FST II · a clinical close-up photograph of a skin lesion · by history, prior malignancy (patient or family), pesticide exposure, and alcohol use:
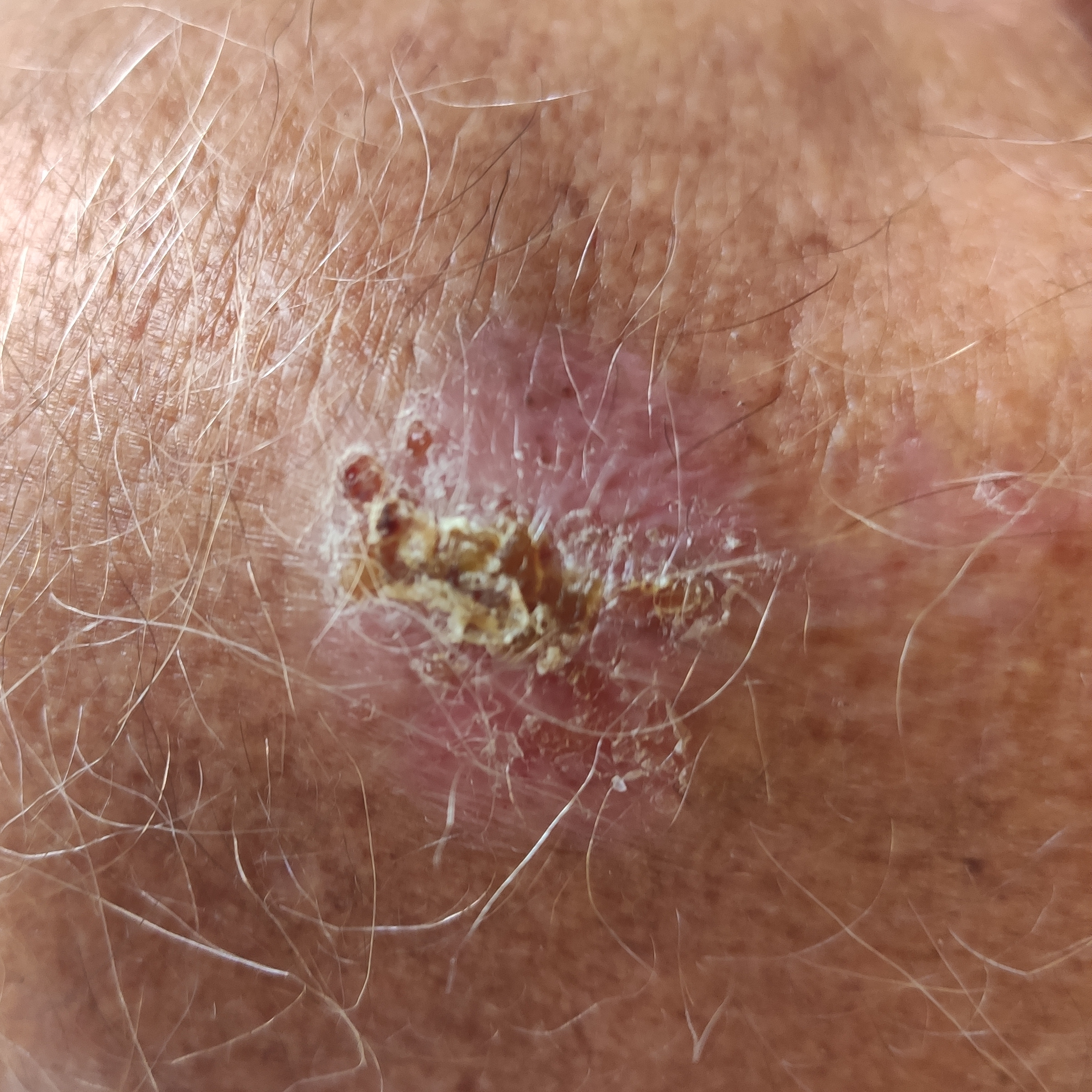The lesion is roughly 40 by 20 mm.
By the patient's account, the lesion has grown, has bled, hurts, is elevated, and itches.
Biopsy-confirmed as a basal cell carcinoma.